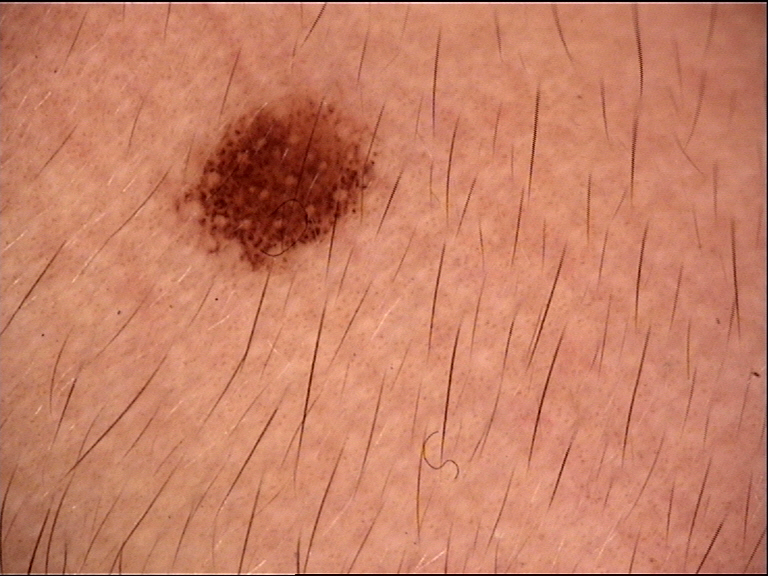Labeled as a compound nevus.